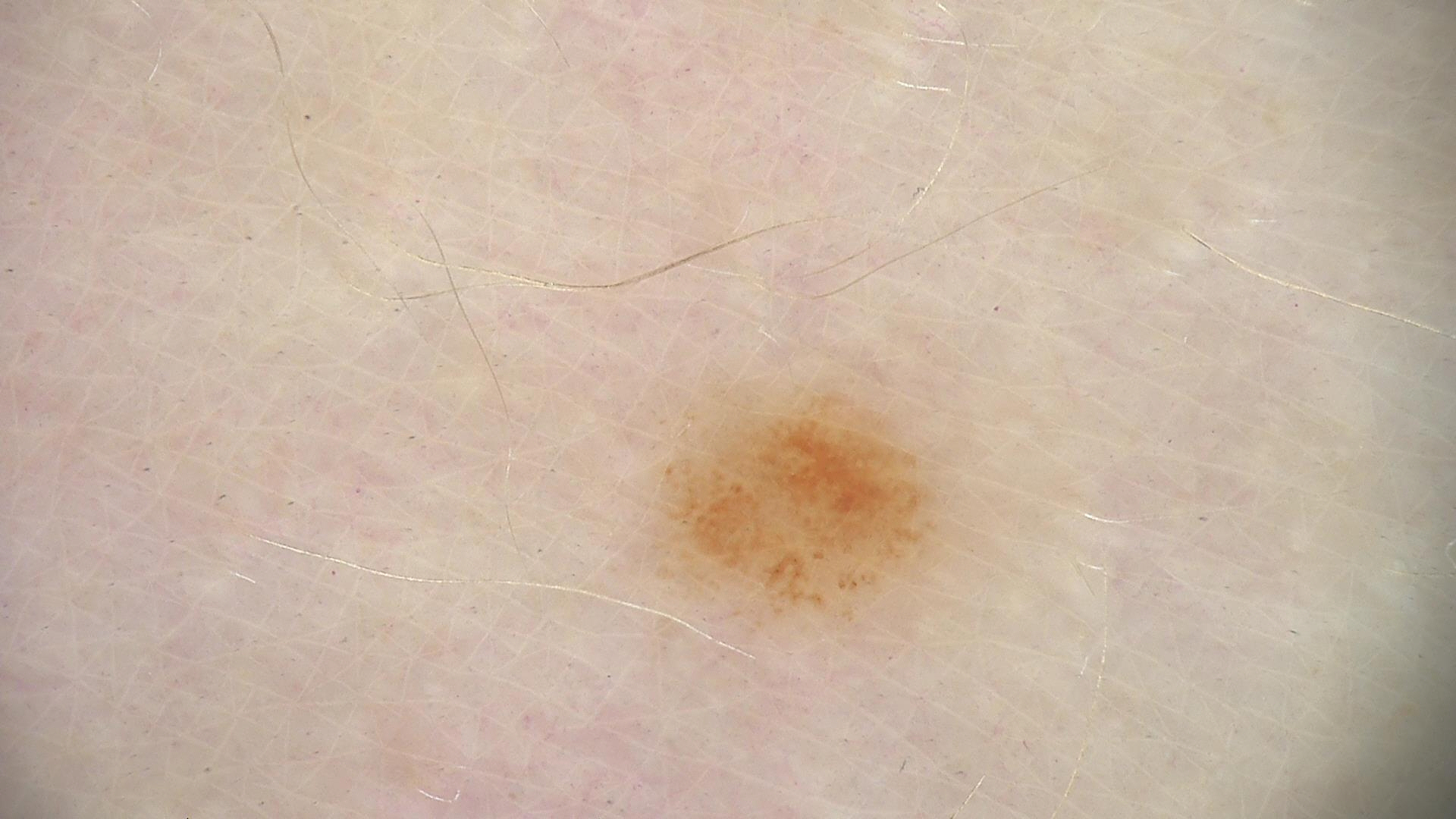Dermoscopy of a skin lesion. The diagnostic label was a benign lesion — a dysplastic junctional nevus.